A dermoscopy image of a single skin lesion.
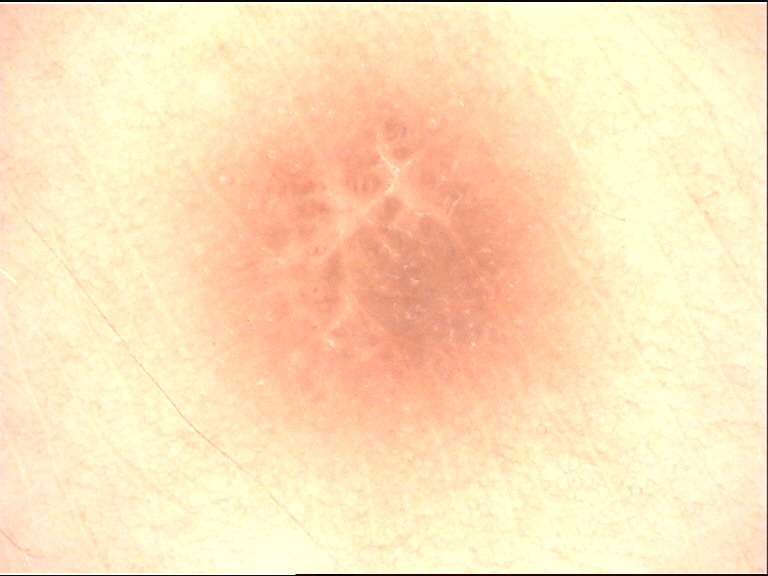Diagnosed as a fibro-histiocytic, benign lesion — a dermatofibroma.